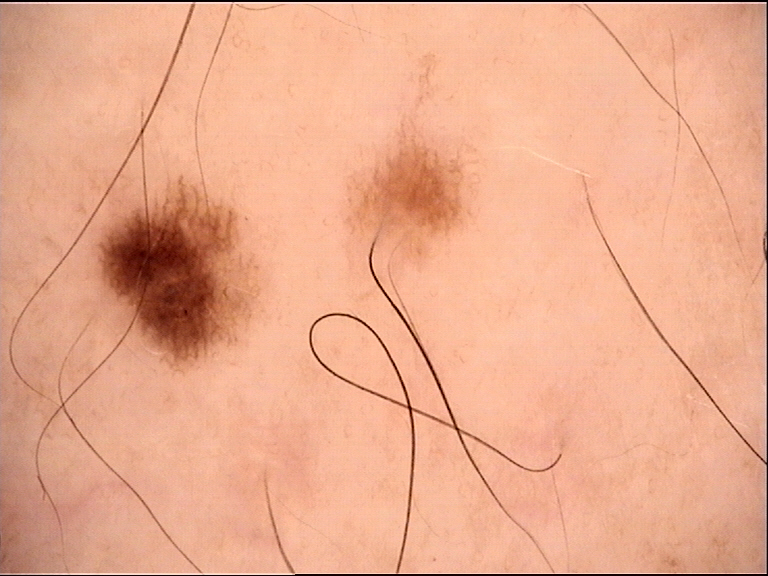A dermoscopy image of a single skin lesion. The diagnosis was a benign lesion — a dysplastic junctional nevus.